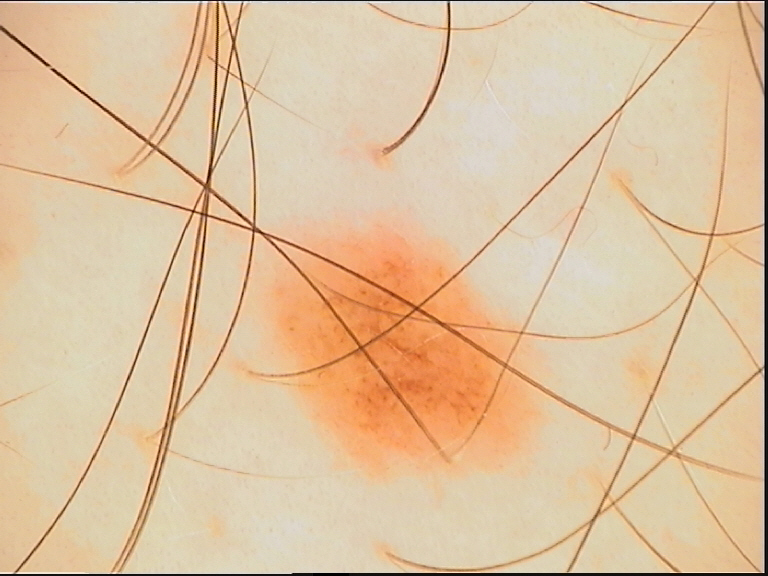{
  "image": "dermoscopy",
  "lesion_type": {
    "main_class": "banal",
    "pattern": "compound"
  },
  "diagnosis": {
    "name": "compound nevus",
    "code": "cb",
    "malignancy": "benign",
    "super_class": "melanocytic",
    "confirmation": "expert consensus"
  }
}